Close-up view.
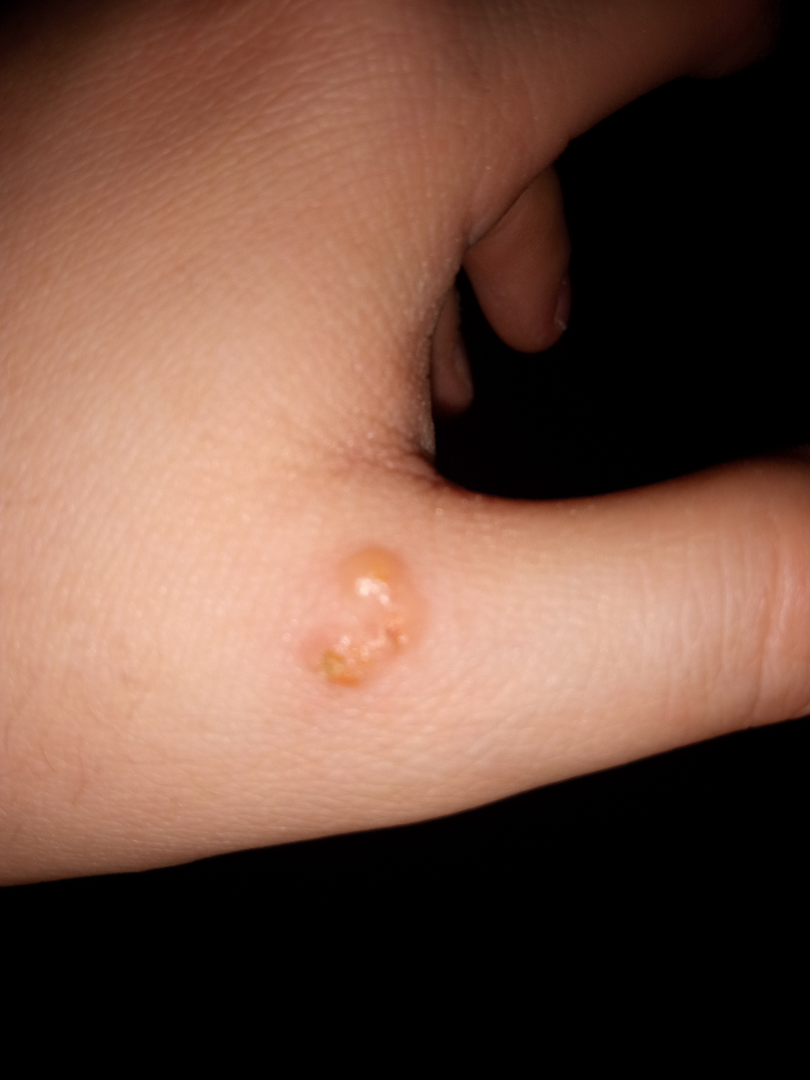The reviewing dermatologist's impression was: Impetigo, Molluscum Contagiosum and Herpes Simplex were considered with similar weight.